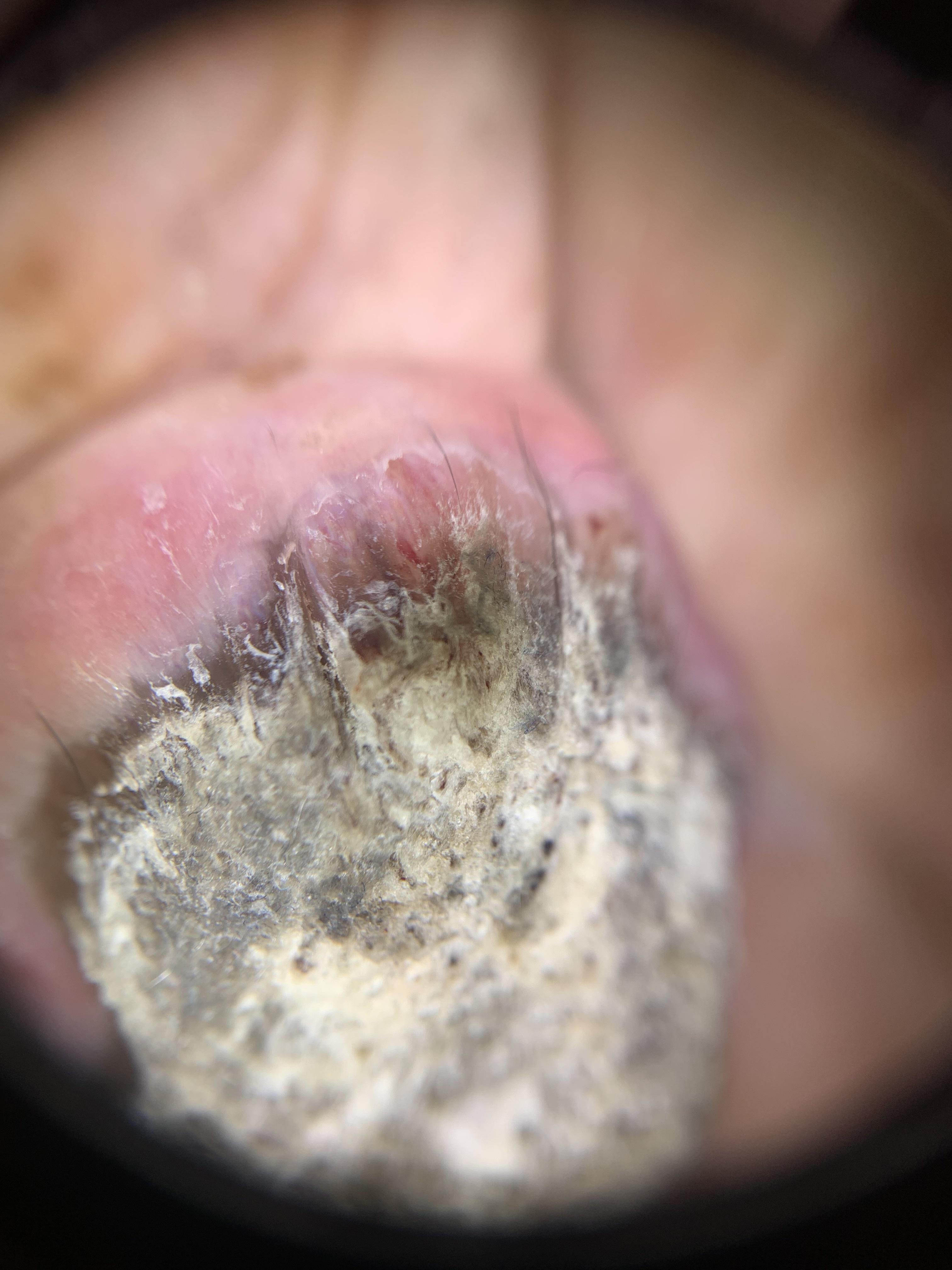Summary: The patient was assessed as FST II. A female patient aged approximately 70. A contact-polarized dermoscopy image of a skin lesion. Conclusion: On biopsy, the diagnosis was a malignancy — a squamous cell carcinoma.